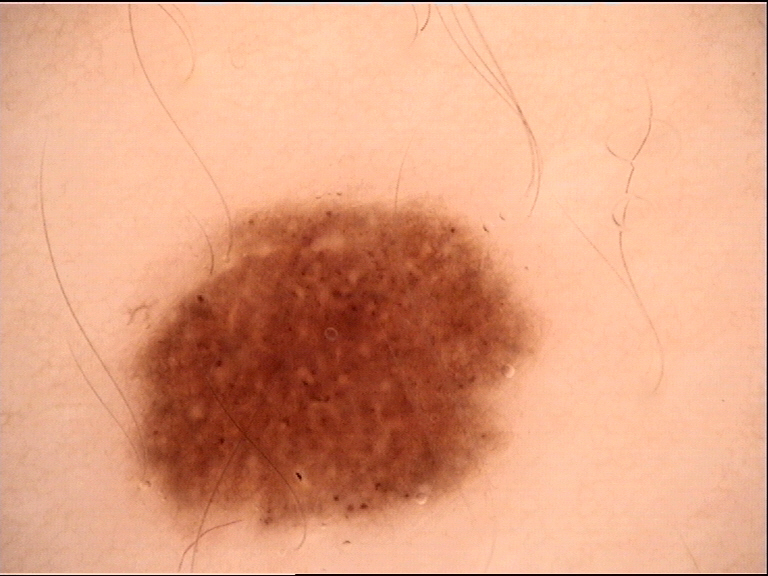Classified as a benign lesion — a dysplastic junctional nevus.